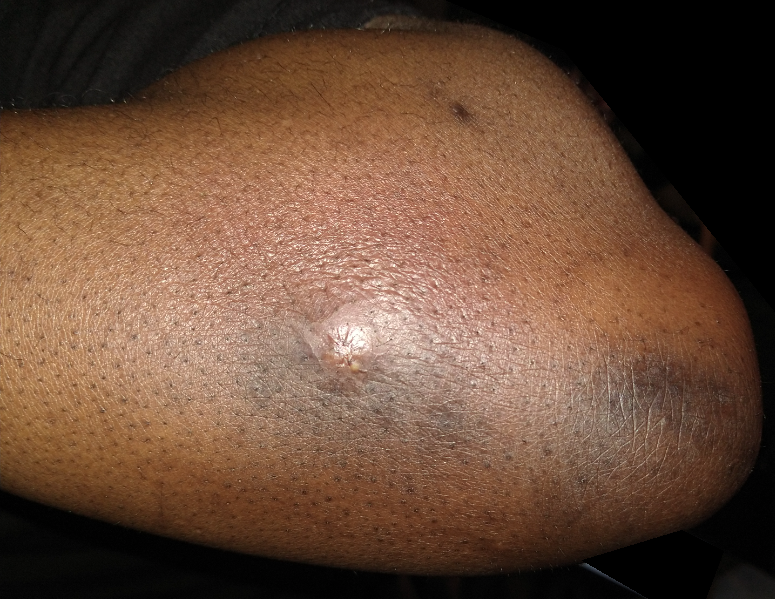Assessment: The case was indeterminate on photographic review. Clinical context: Located on the arm. Close-up view. The contributor notes bothersome appearance, itching and enlargement. No constitutional symptoms were reported. The contributor notes the lesion is raised or bumpy, rough or flaky and fluid-filled.